The affected area is the leg, back of the torso and front of the torso; the contributor is a female aged 18–29; the photo was captured at an angle: 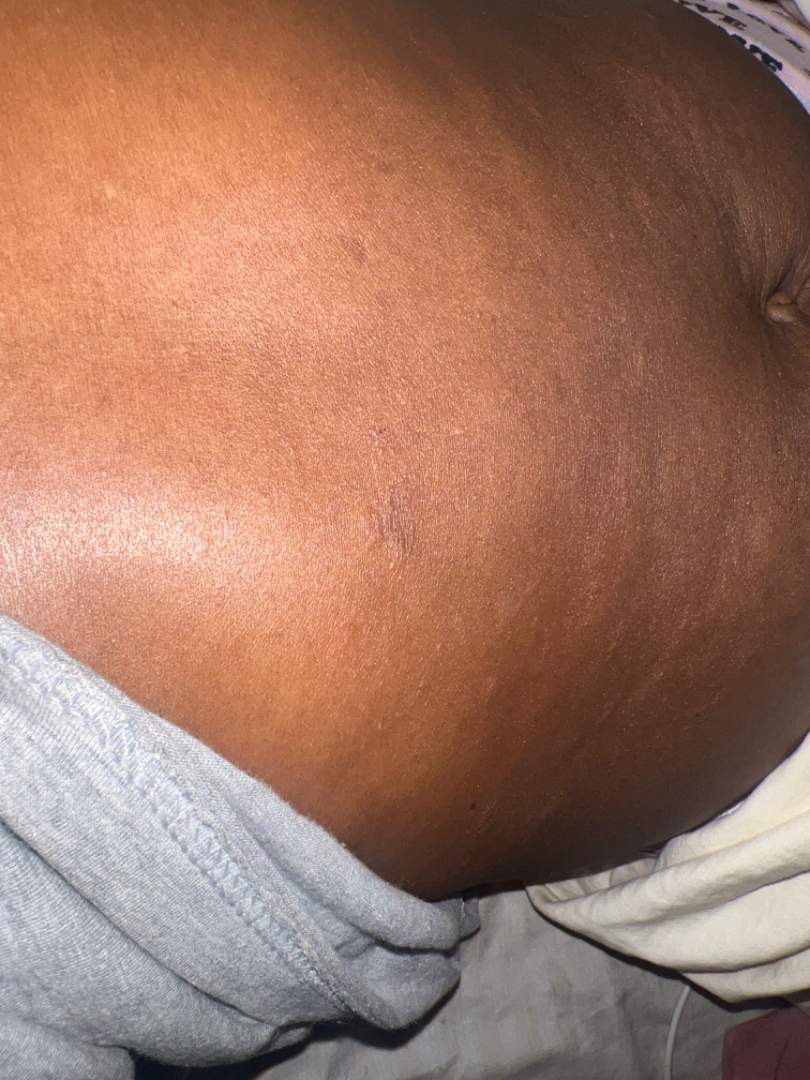Findings: The primary impression is Pityriasis rosea; also raised was Eczema.